A close-up photograph; the affected area is the back of the hand; the subject is male.
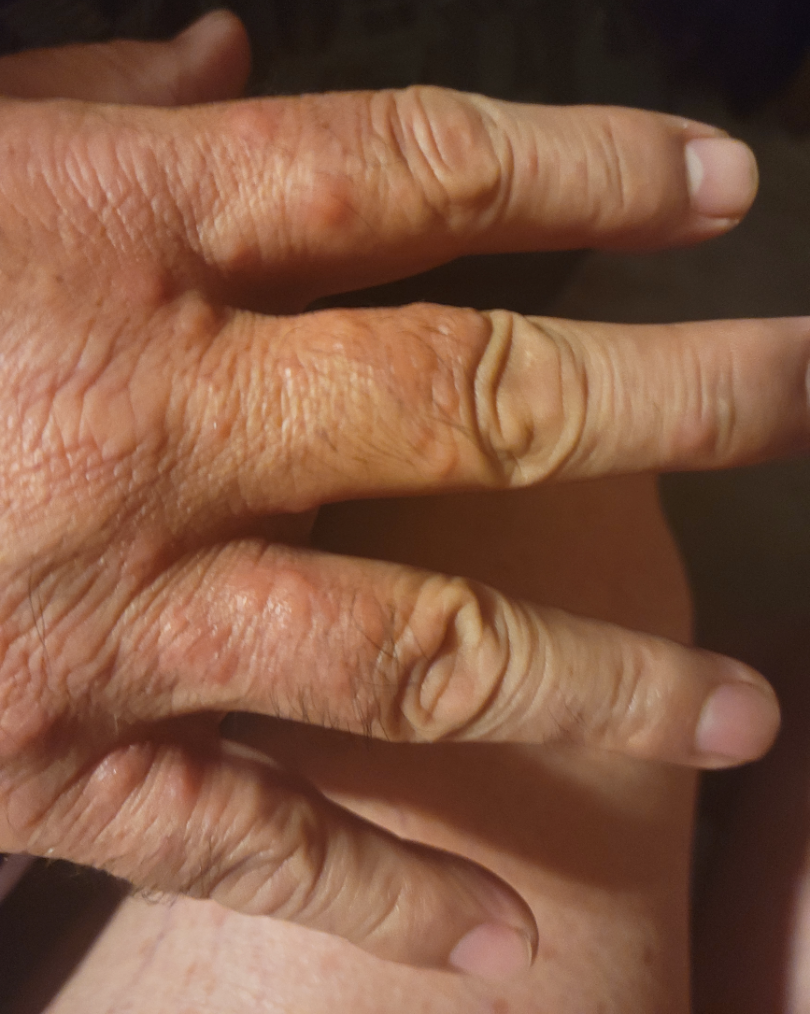{"differential": {"tied_lead": ["Histiocytosis of skin", "Insect Bite"], "considered": ["Lichenoid myxedema"]}}